A dermatoscopic image of a skin lesion.
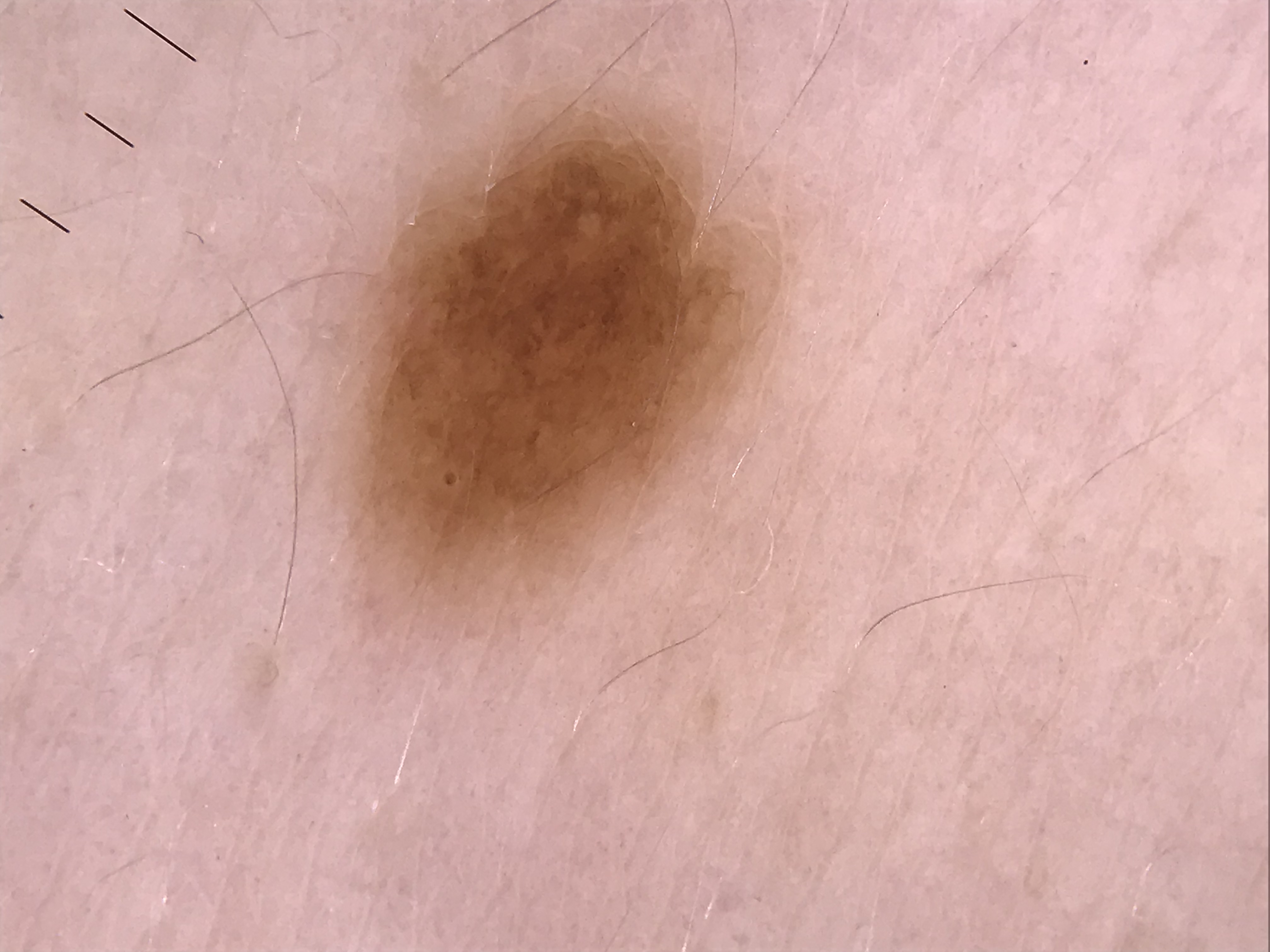{"lesion_type": {"main_class": "banal", "pattern": "junctional"}, "diagnosis": {"name": "junctional nevus", "code": "jb", "malignancy": "benign", "super_class": "melanocytic", "confirmation": "expert consensus"}}